A dermatoscopic image of a skin lesion.
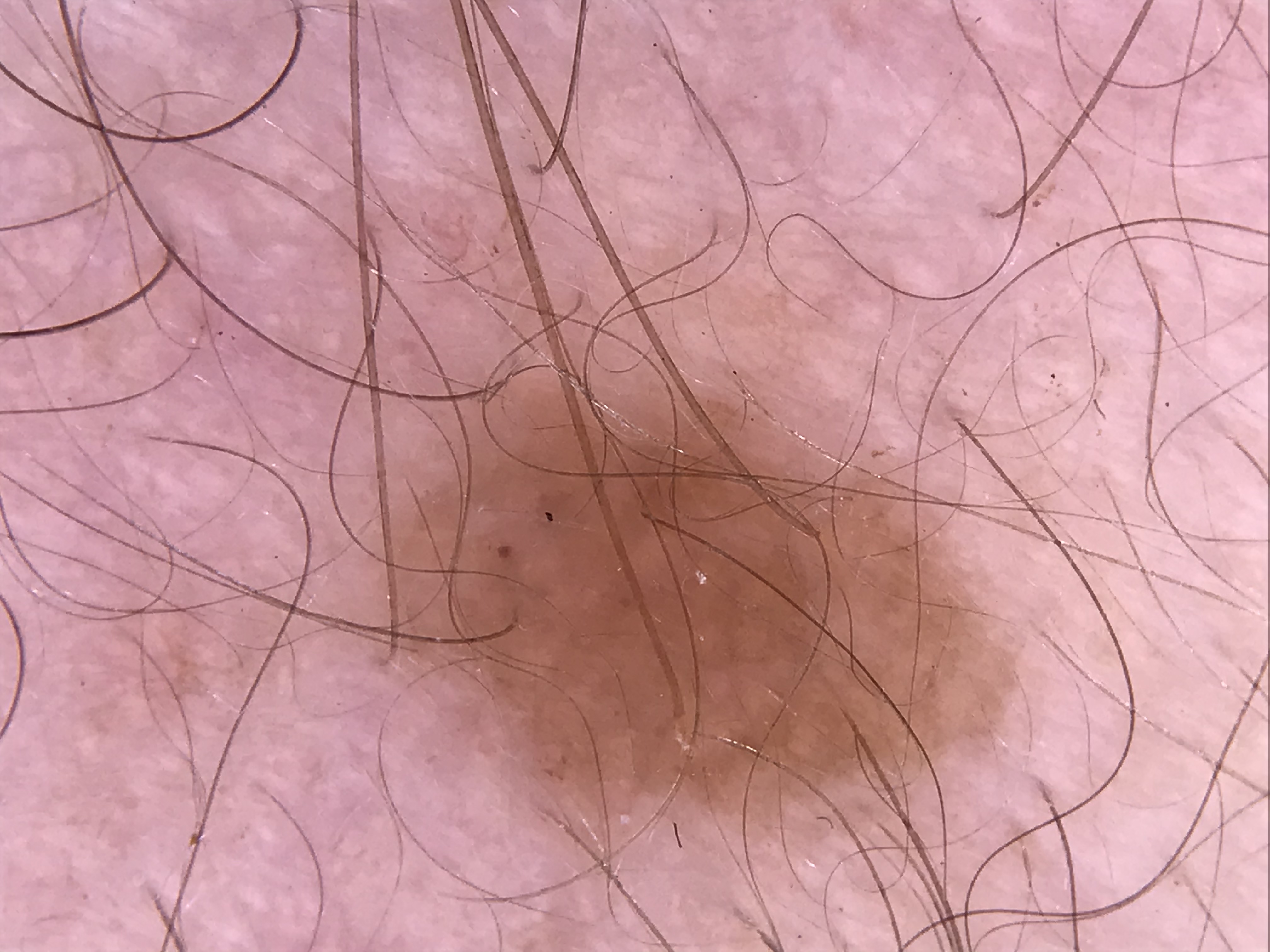Diagnosed as a banal lesion — a junctional nevus.